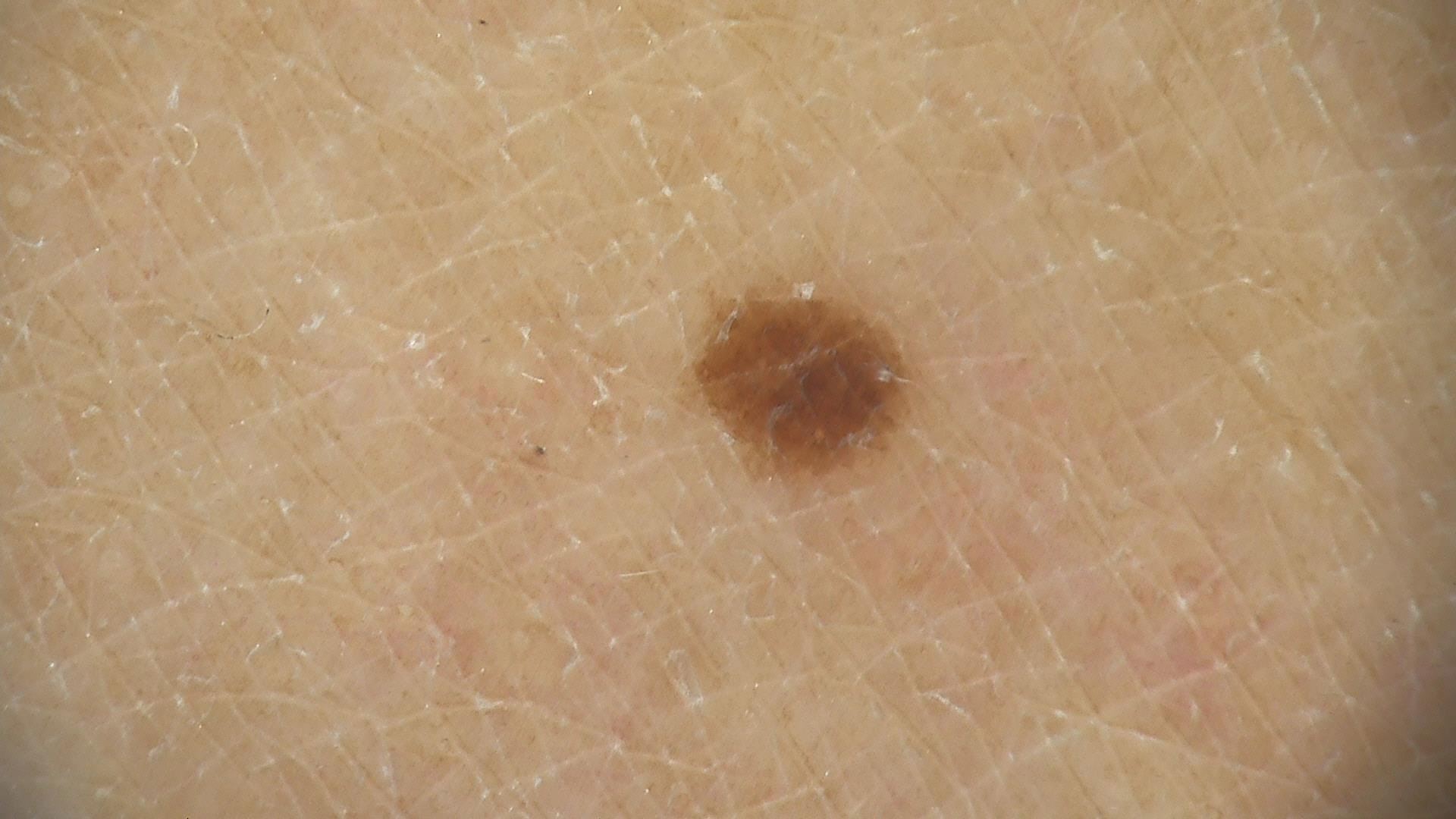Findings:
– image · dermoscopy
– classification · banal
– label · junctional nevus (expert consensus)